Located on the arm · the photograph is a close-up of the affected area: 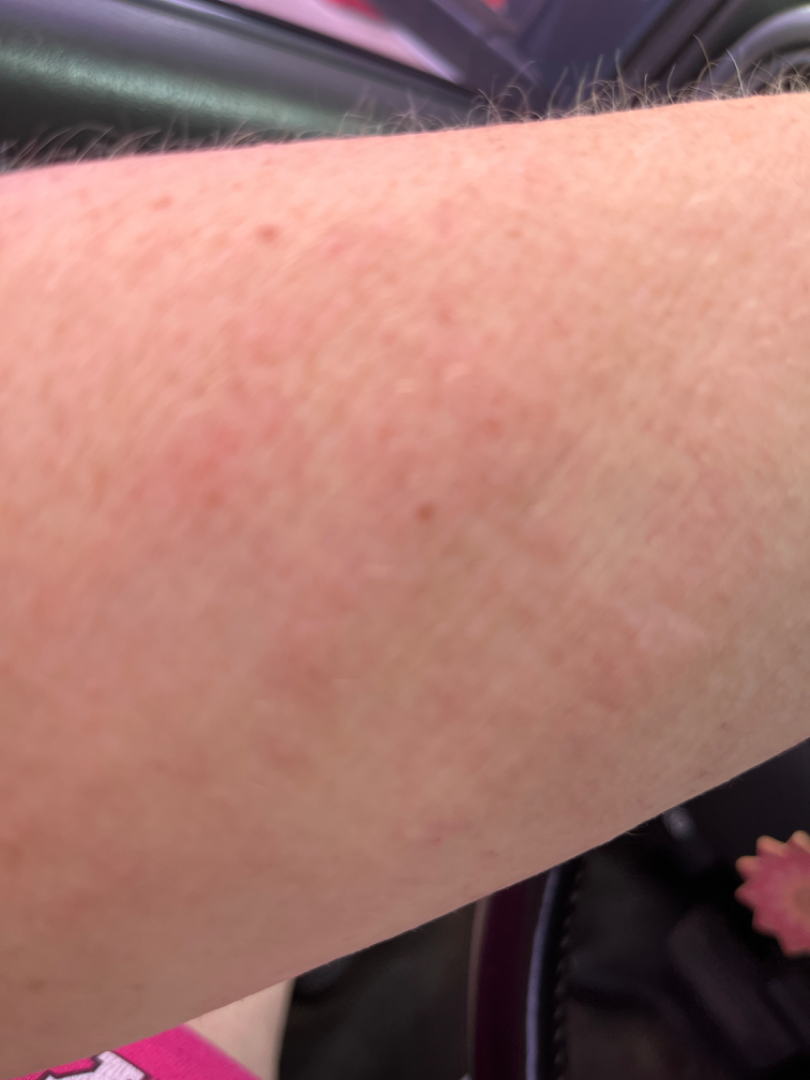No differential diagnosis could be assigned on photographic review. The lesion is associated with itching and burning. Texture is reported as raised or bumpy. Skin tone: FST II. The patient considered this a rash. The contributor reports the condition has been present for one to four weeks.